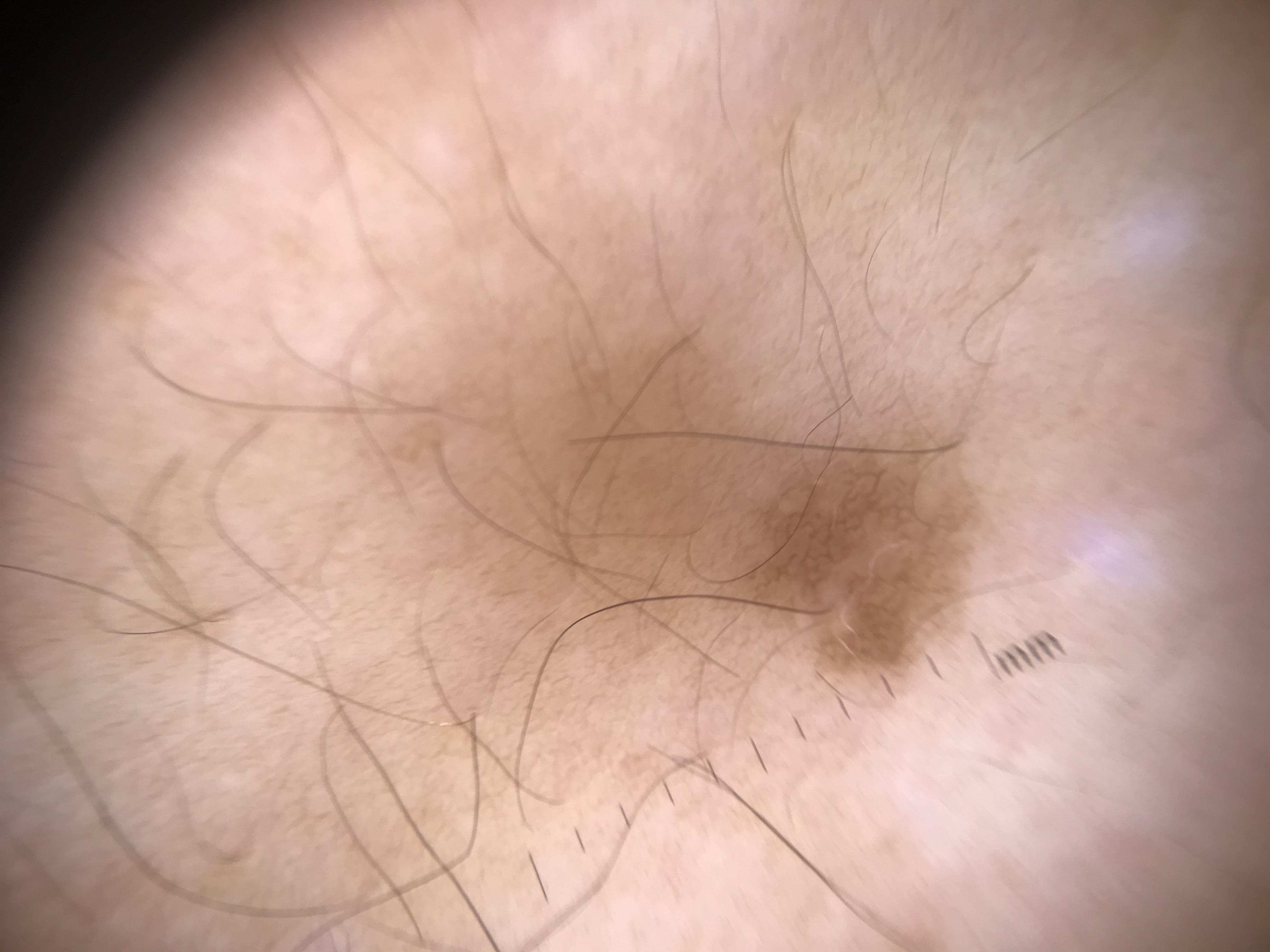{"image": "dermoscopy", "diagnosis": {"name": "junctional nevus", "code": "jb", "malignancy": "benign", "super_class": "melanocytic", "confirmation": "expert consensus"}}